The subject is a female aged 30–39 · an image taken at an angle · the affected area is the leg — 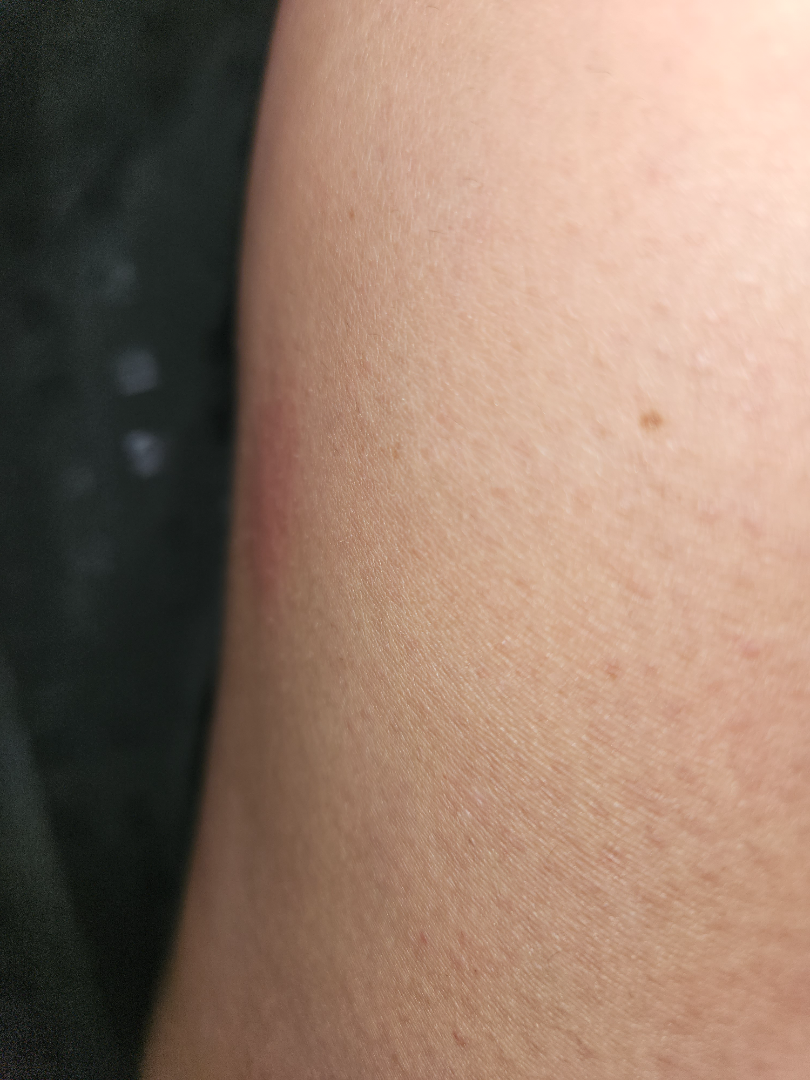differential diagnosis = Pigmented purpuric eruption, Drug Rash and Eczema were each considered, in no particular order